The photo was captured at a distance.
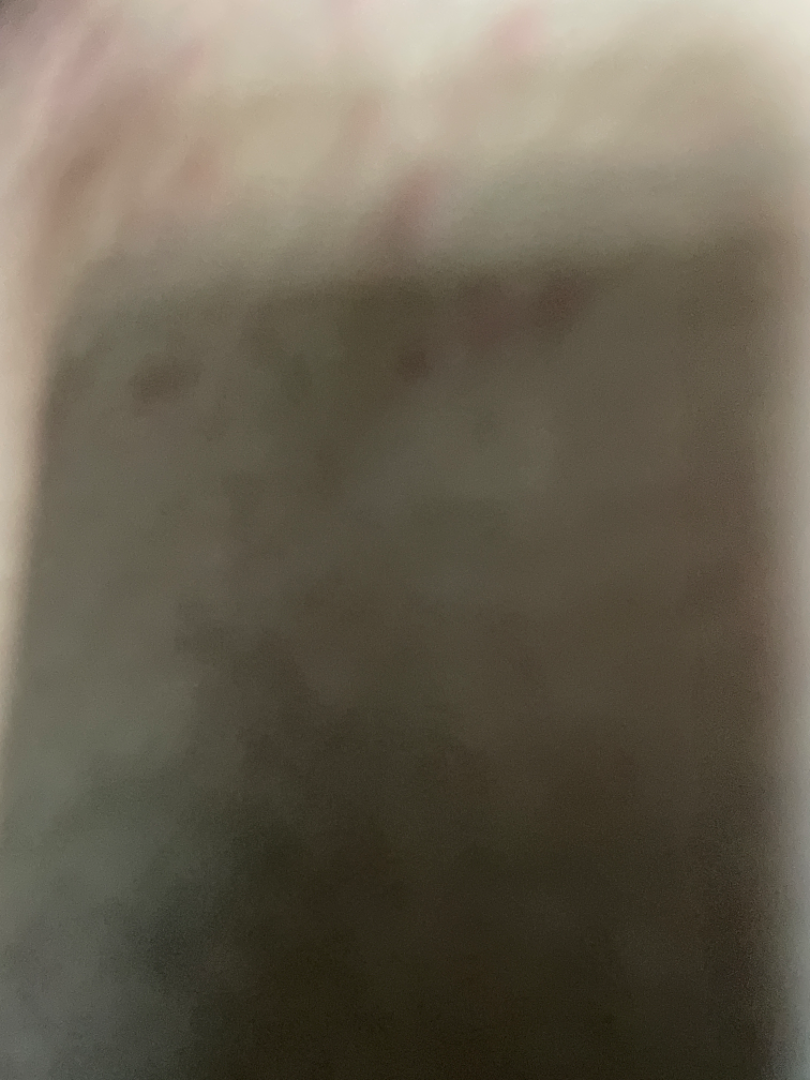Assessment: One reviewing dermatologist: the differential is split between Folliculitis, Insect Bite and Allergic Contact Dermatitis.